A dermoscopic close-up of a skin lesion: 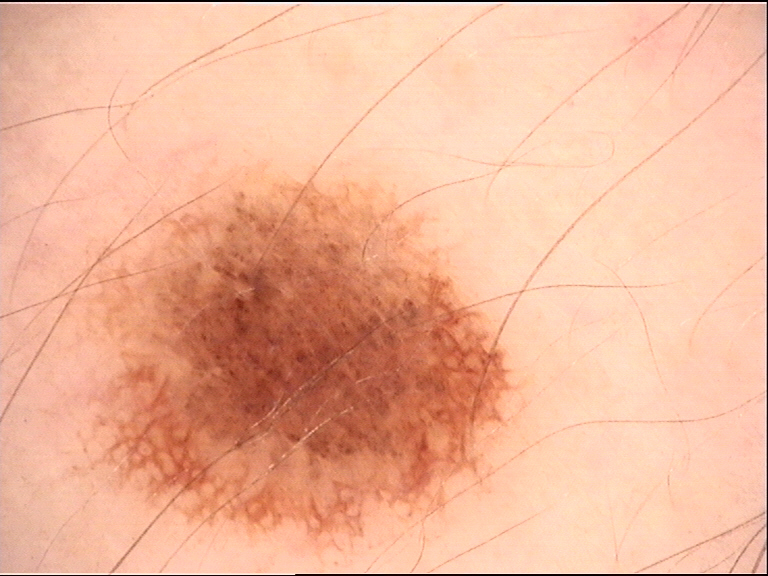<dermoscopy>
  <diagnosis>
    <name>dysplastic junctional nevus</name>
    <code>jd</code>
    <malignancy>benign</malignancy>
    <super_class>melanocytic</super_class>
    <confirmation>expert consensus</confirmation>
  </diagnosis>
</dermoscopy>